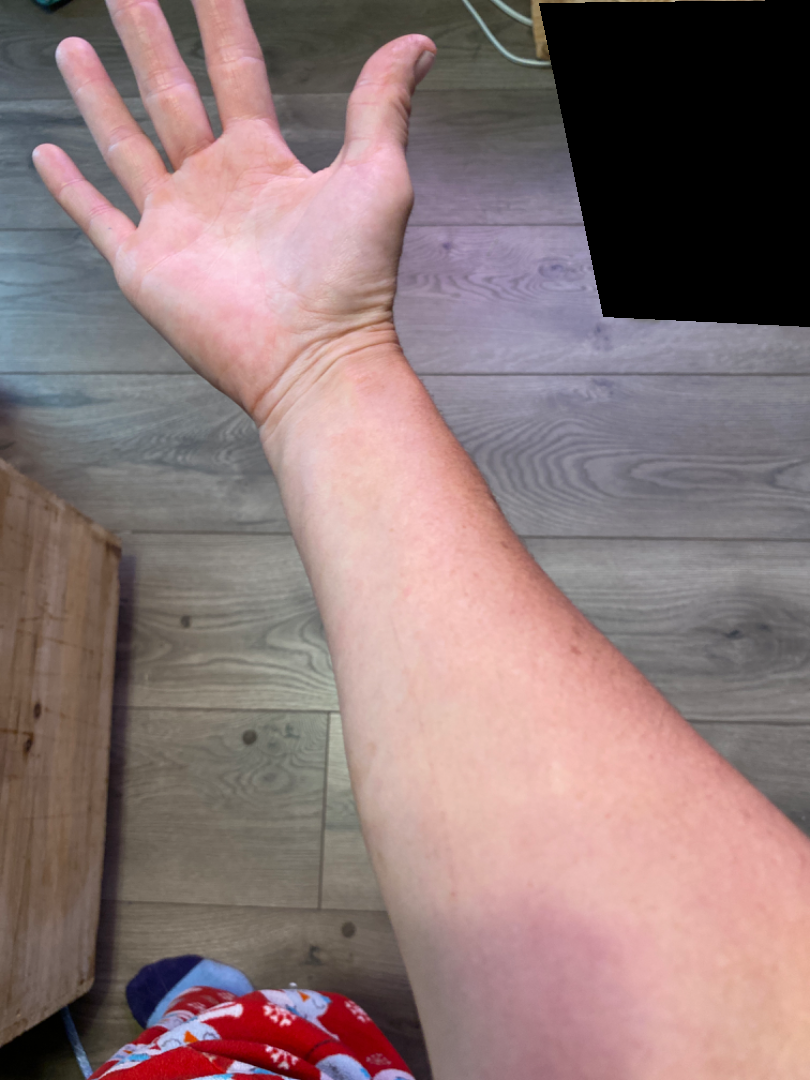Notes:
- affected area — back of the hand and arm
- patient describes the issue as — a rash
- other reported symptoms — none reported
- history — about one day
- view — at a distance
- patient — female, age 40–49
- clinical impression — three independent reviewers: the leading consideration is Eczema; possibly Allergic Contact Dermatitis